A dermoscopy image of a single skin lesion.
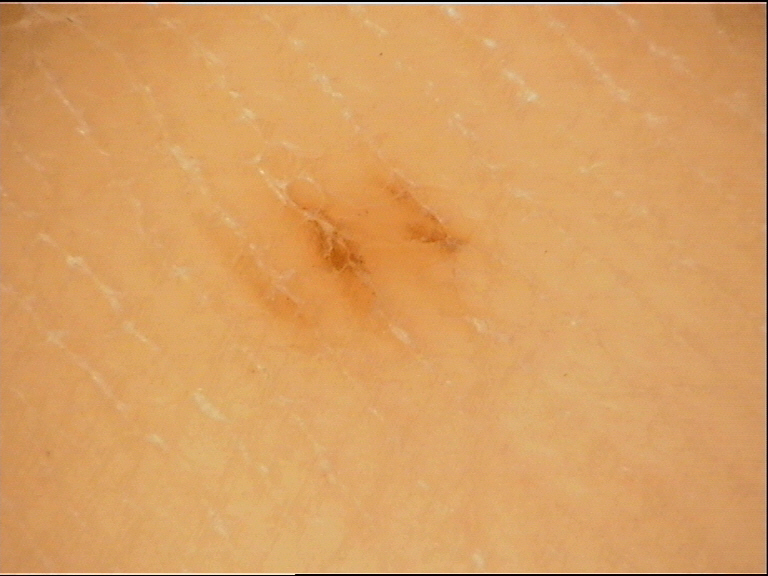Case:
- assessment — acral junctional nevus (expert consensus)